A dermatoscopic image of a skin lesion.
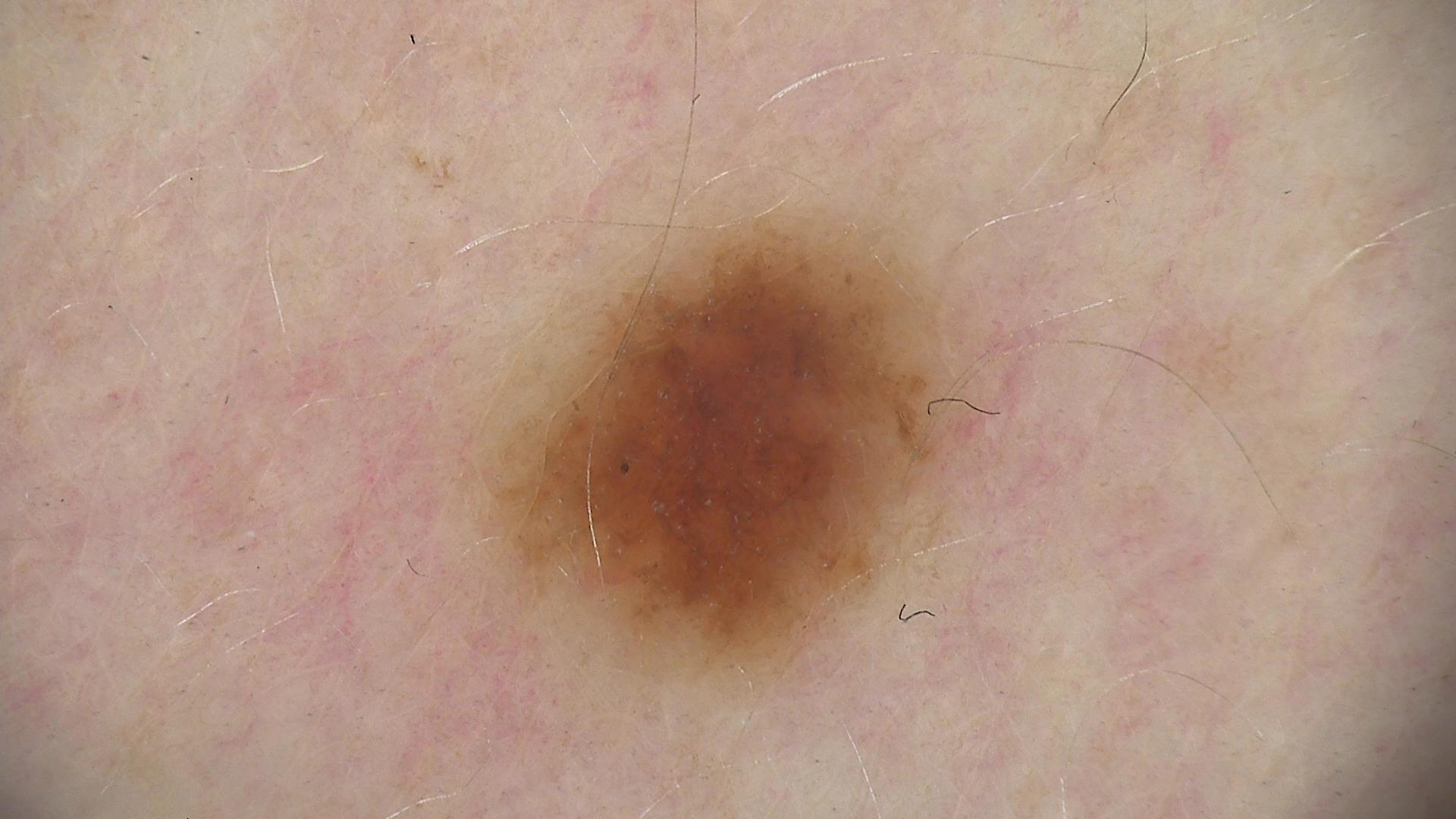Consistent with a dysplastic junctional nevus.